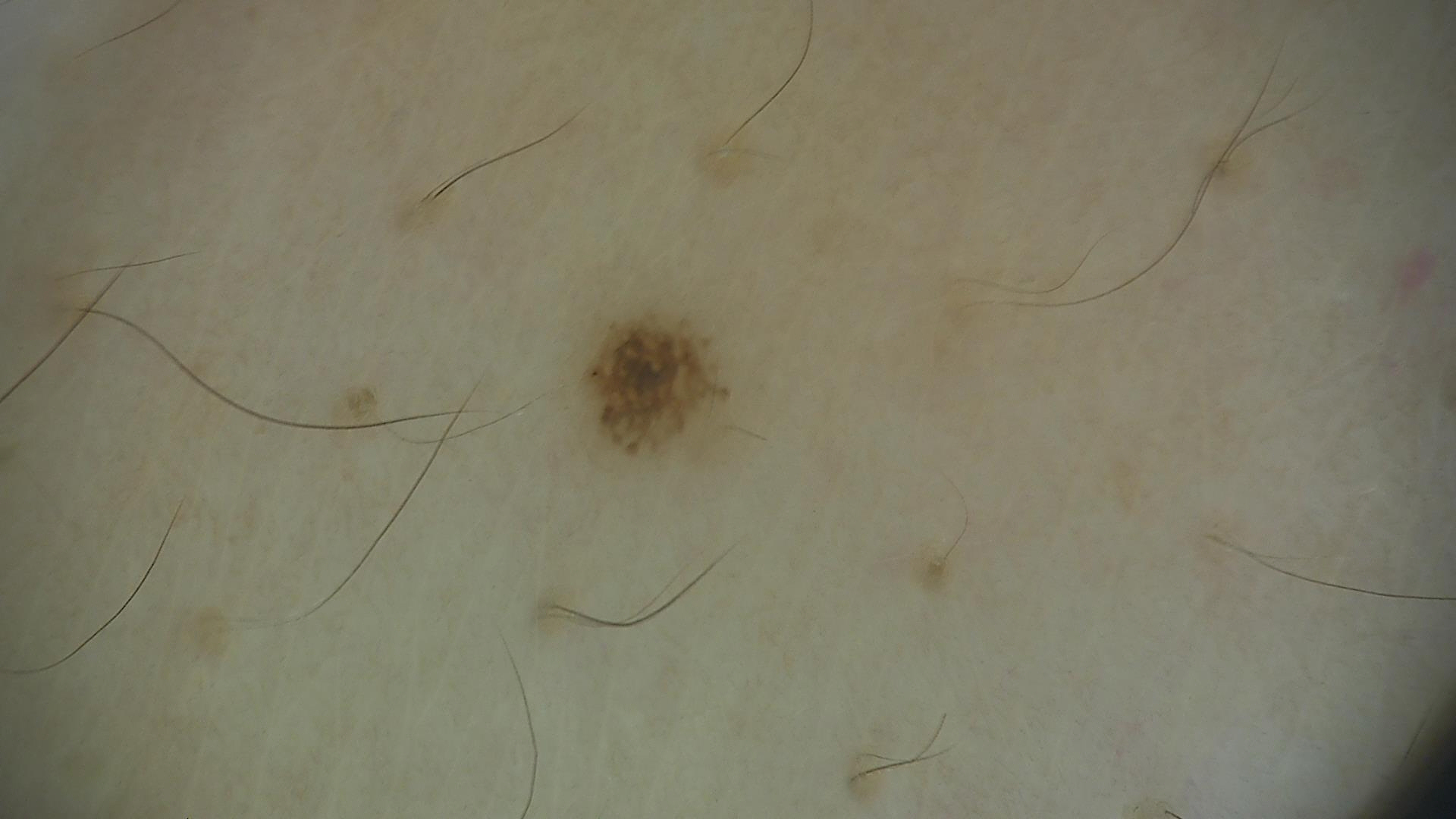Impression:
Labeled as a dysplastic junctional nevus.